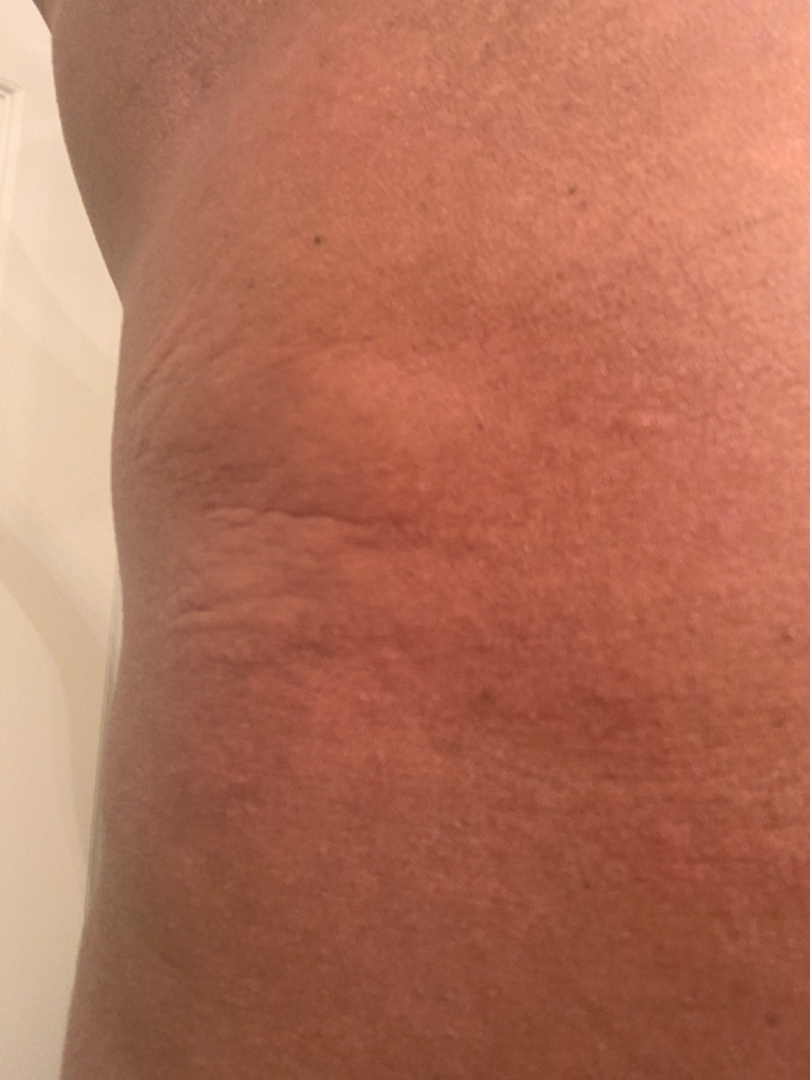History:
The patient described the issue as a growth or mole. The contributor notes enlargement, itching and bothersome appearance. The photo was captured at a distance. Male subject, age 30–39. Located on the front of the torso and leg. The condition has been present for about one day. The lesion is described as raised or bumpy. The contributor notes associated joint pain.
Impression:
Most likely Urticaria; less likely is Allergic Contact Dermatitis.